The photo was captured at an angle.
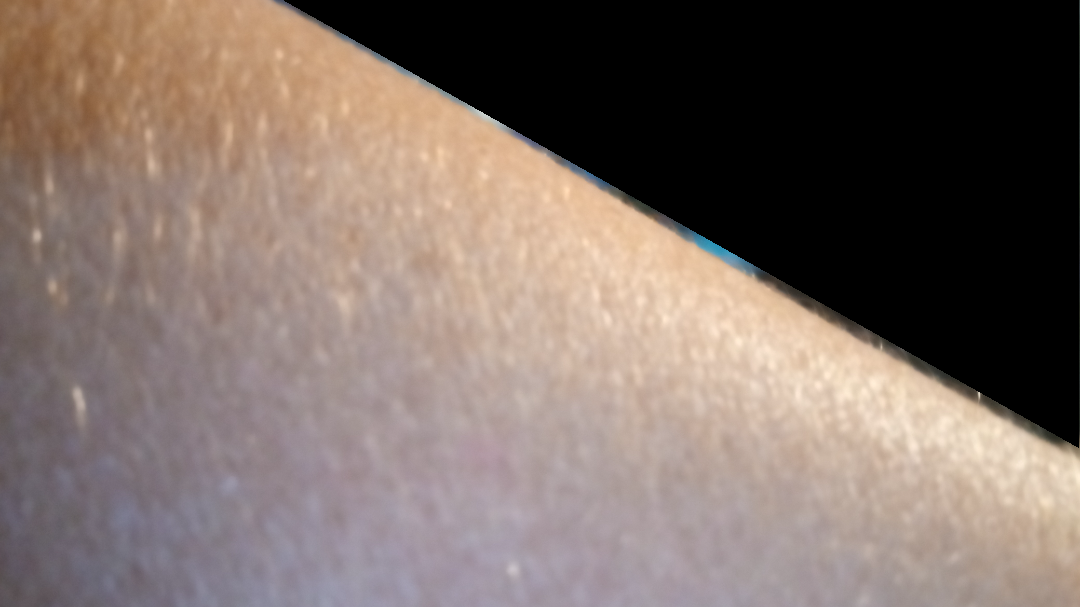No discernible pathology was noted by the reviewing dermatologist. Fitzpatrick skin type IV.